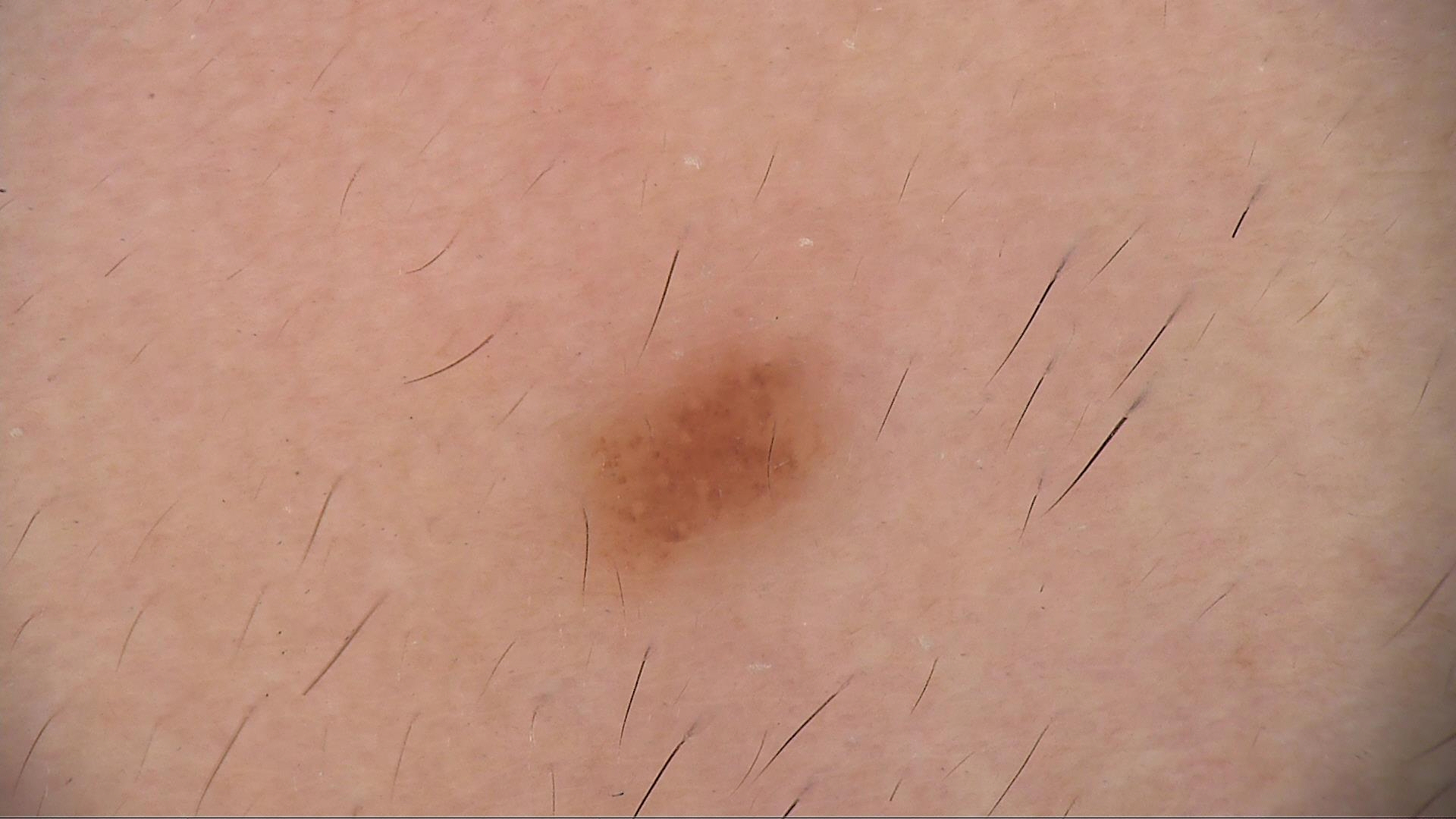class — junctional nevus (expert consensus).